The subject is a female aged 18–29, the affected area is the head or neck, close-up view — 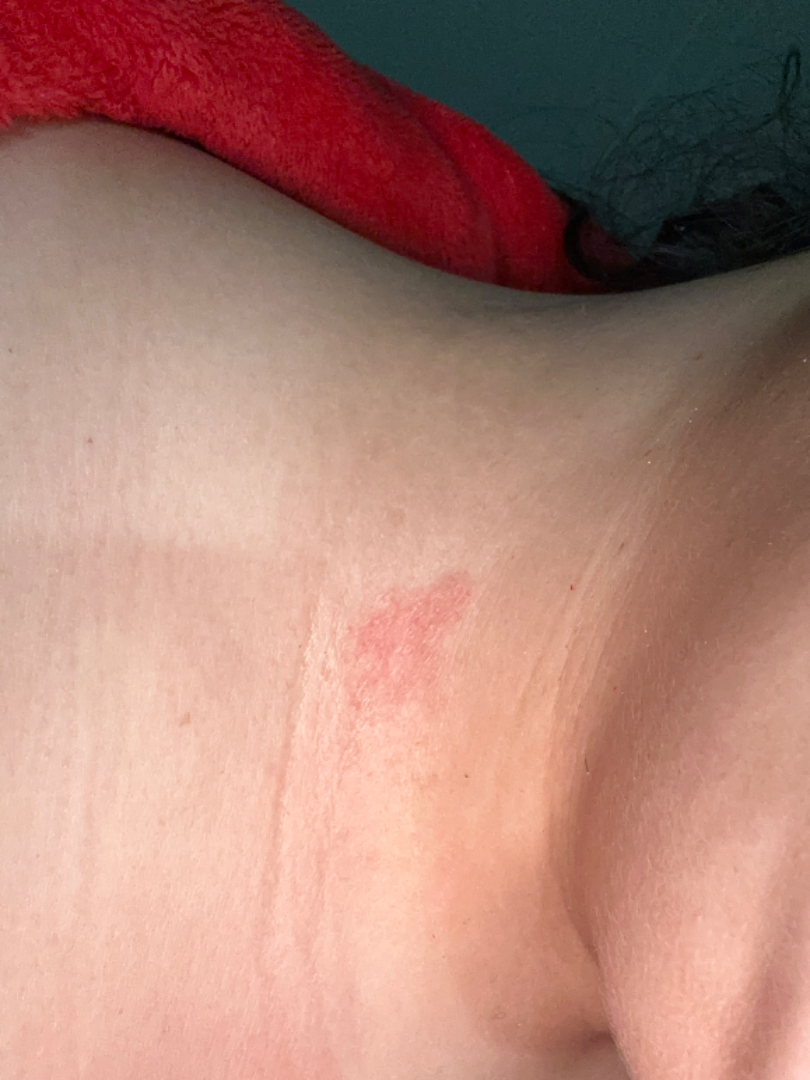The reviewing dermatologist's impression was: most likely Eczema; also consider Tinea; also on the differential is Allergic Contact Dermatitis.